Female contributor, age 18–29. The affected area is the back of the hand. An image taken at a distance: 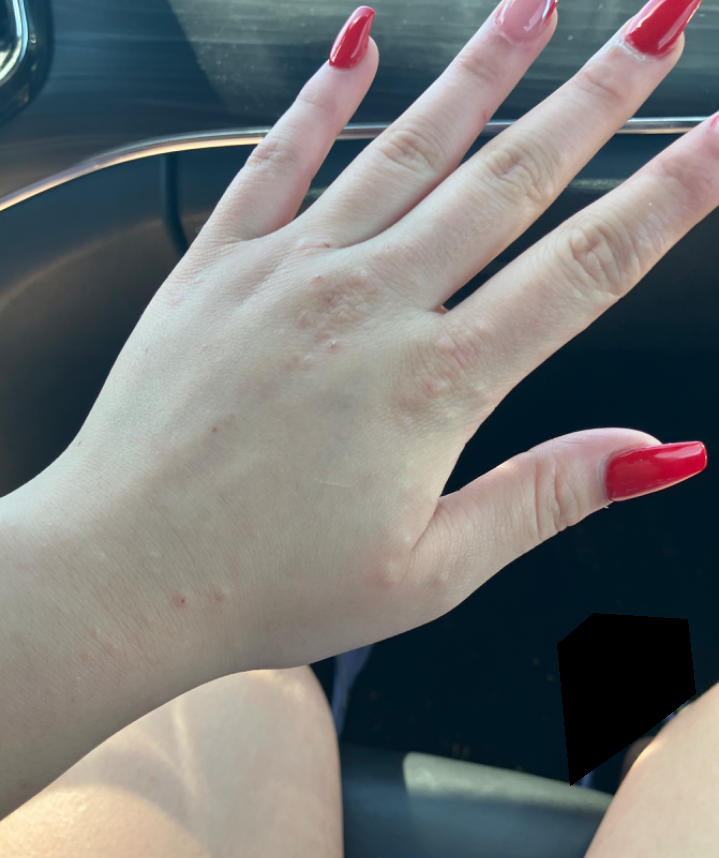The condition could not be reliably identified from the image. The lesion is described as rough or flaky, raised or bumpy and fluid-filled. The patient considered this a rash. Present for one to four weeks. Skin tone: FST II. Symptoms reported: burning, pain, bothersome appearance, itching and enlargement.